The chart notes prior skin cancer (patient or family) and prior malignancy (patient or family); a female subject 88 years old; a clinical close-up photograph of a skin lesion; skin type II — 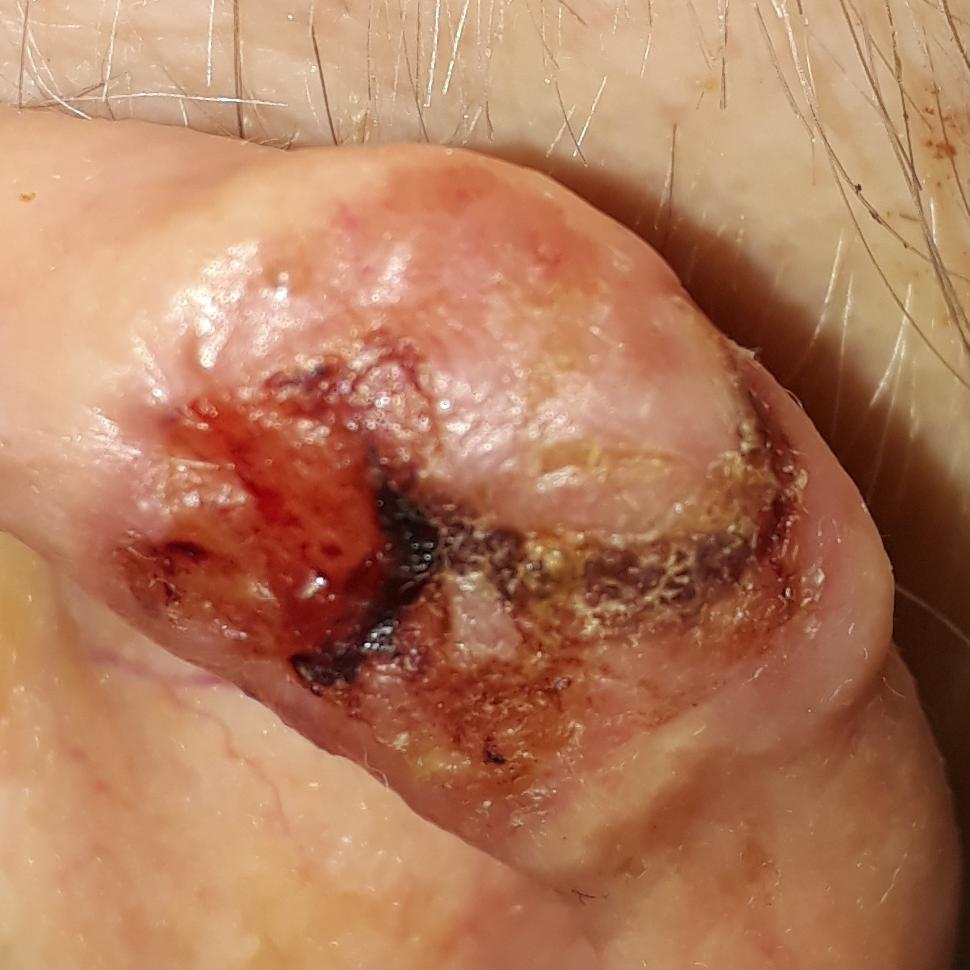Case:
* site: an ear
* lesion diameter: 13x10 mm
* reported symptoms: pain, growth, elevation, itching, bleeding
* pathology: basal cell carcinoma (biopsy-proven)